A dermoscopic photograph of a skin lesion.
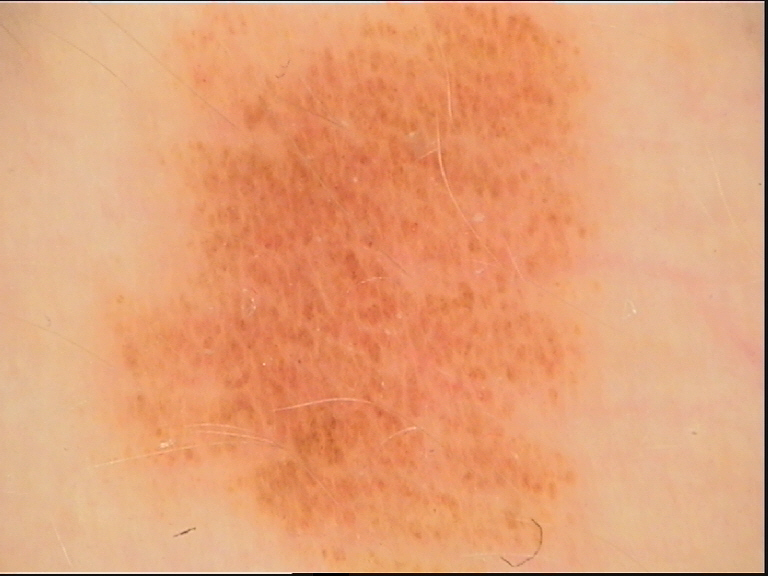Impression: Consistent with a dysplastic junctional nevus.